The subject is 30–39, female. The leg is involved. An image taken at a distance: 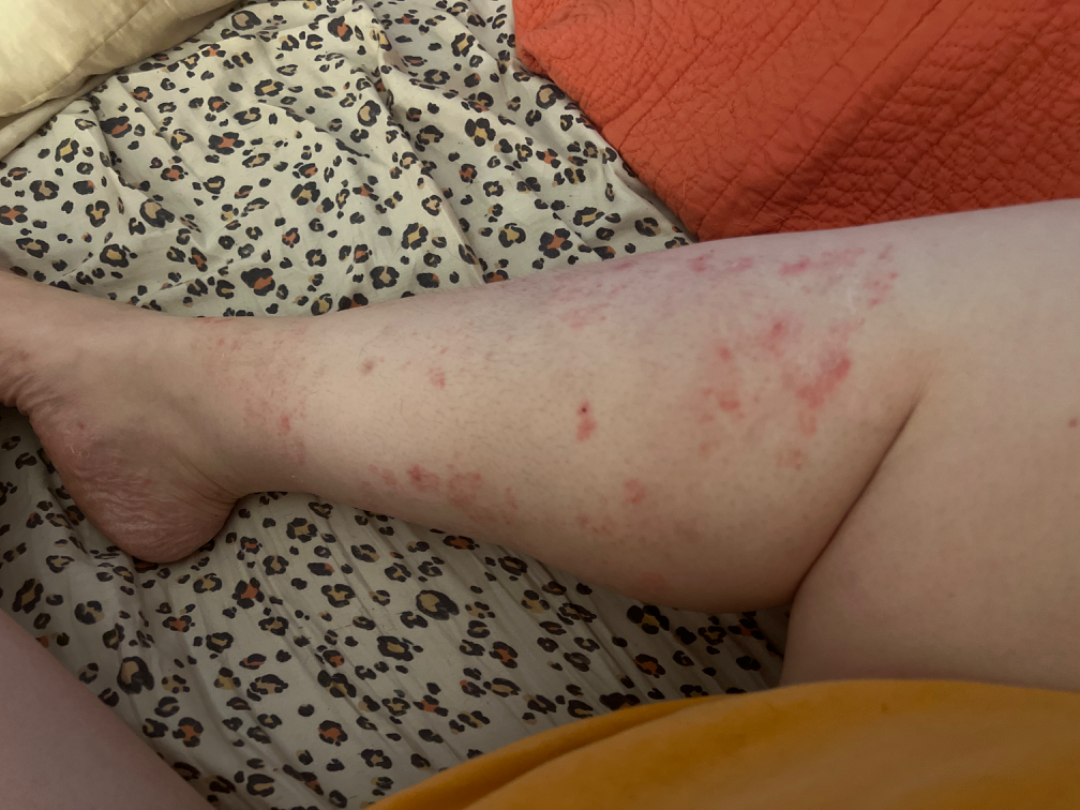The patient reported no systemic symptoms. The contributor reports enlargement, burning, itching, bothersome appearance and pain. The patient considered this a rash. The condition has been present for more than one year. The contributor reports the lesion is rough or flaky, flat and raised or bumpy. Most likely Tinea; also on the differential is Eczema.